Dermoscopy of a skin lesion.
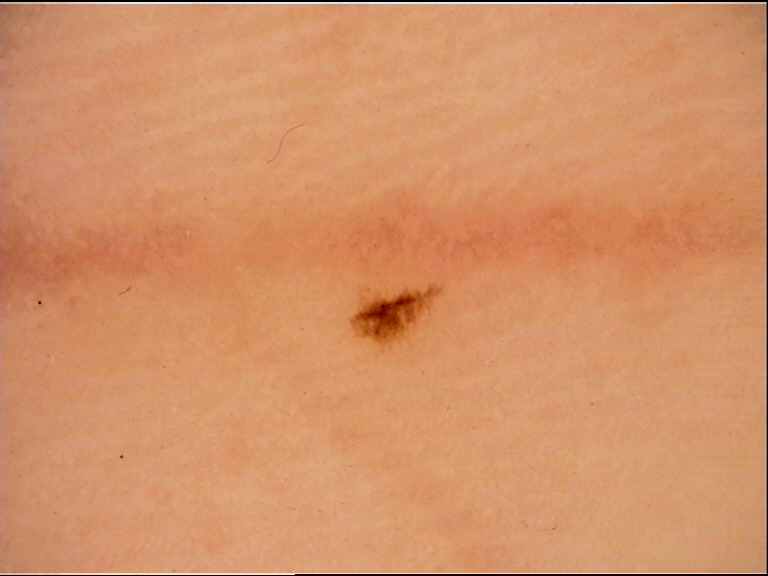Q: What was the diagnostic impression?
A: acral dysplastic junctional nevus (expert consensus)